This is a close-up image:
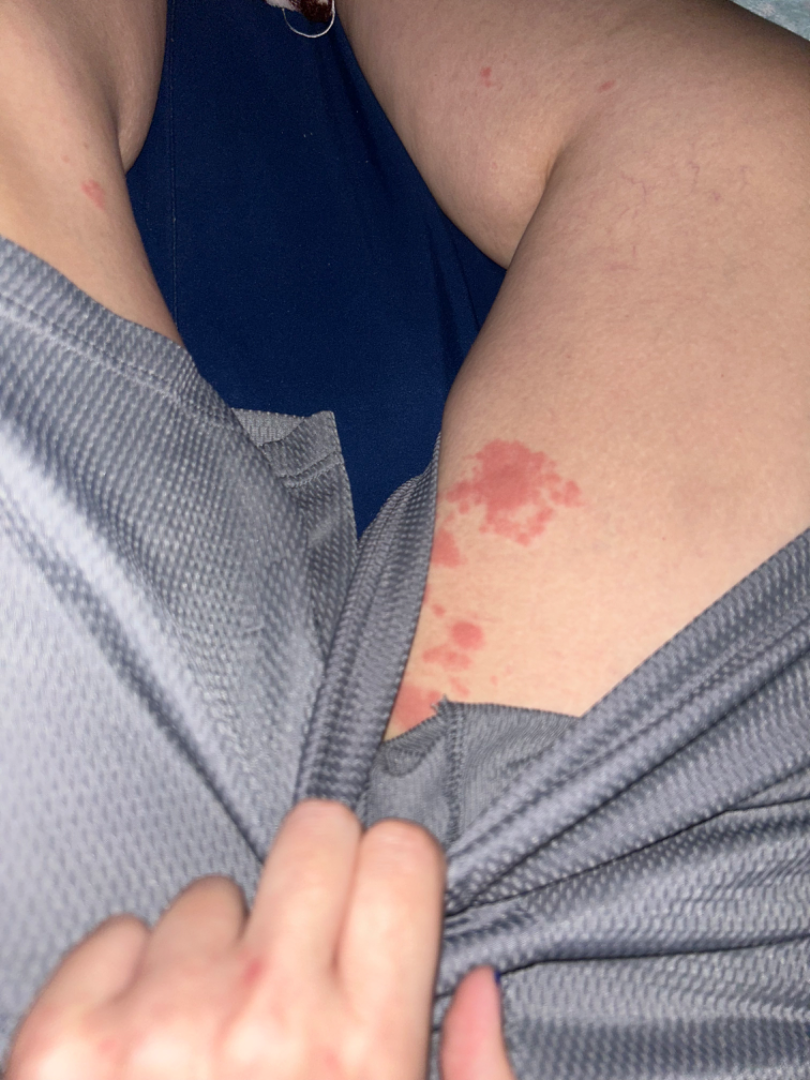| key | value |
|---|---|
| clinical impression | a single dermatologist reviewed the case: the leading consideration is Tinea; also on the differential is Candidal intertrigo; possibly Erythema multiforme |